A dermatoscopic image of a skin lesion.
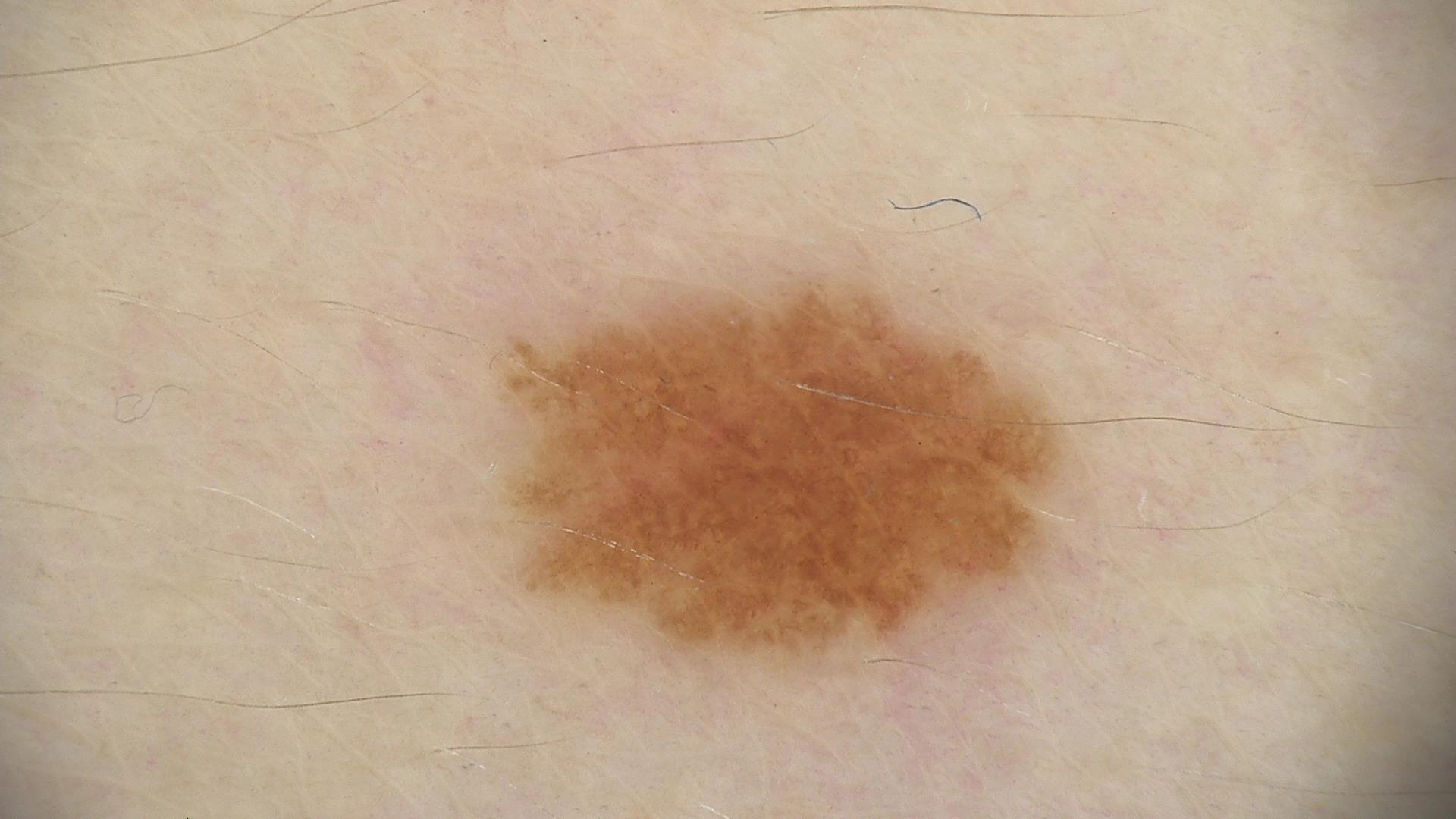Diagnosed as a dysplastic junctional nevus.